By history, prior malignancy (patient or family) and no prior skin cancer (patient or family). Fitzpatrick skin type III — 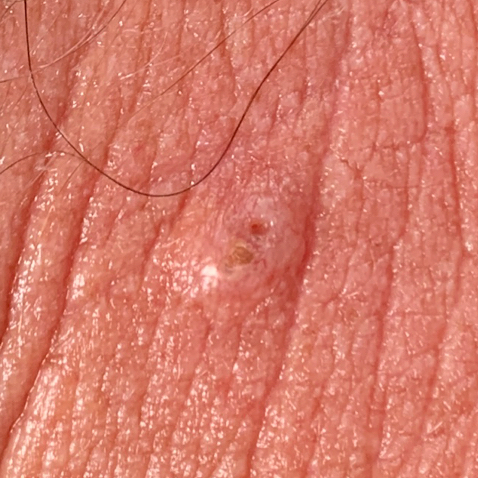Q: What is the anatomic site?
A: the neck
Q: How large is the lesion?
A: 9x5 mm
Q: What is this lesion?
A: basal cell carcinoma (biopsy-proven)